A dermatoscopic image of a skin lesion.
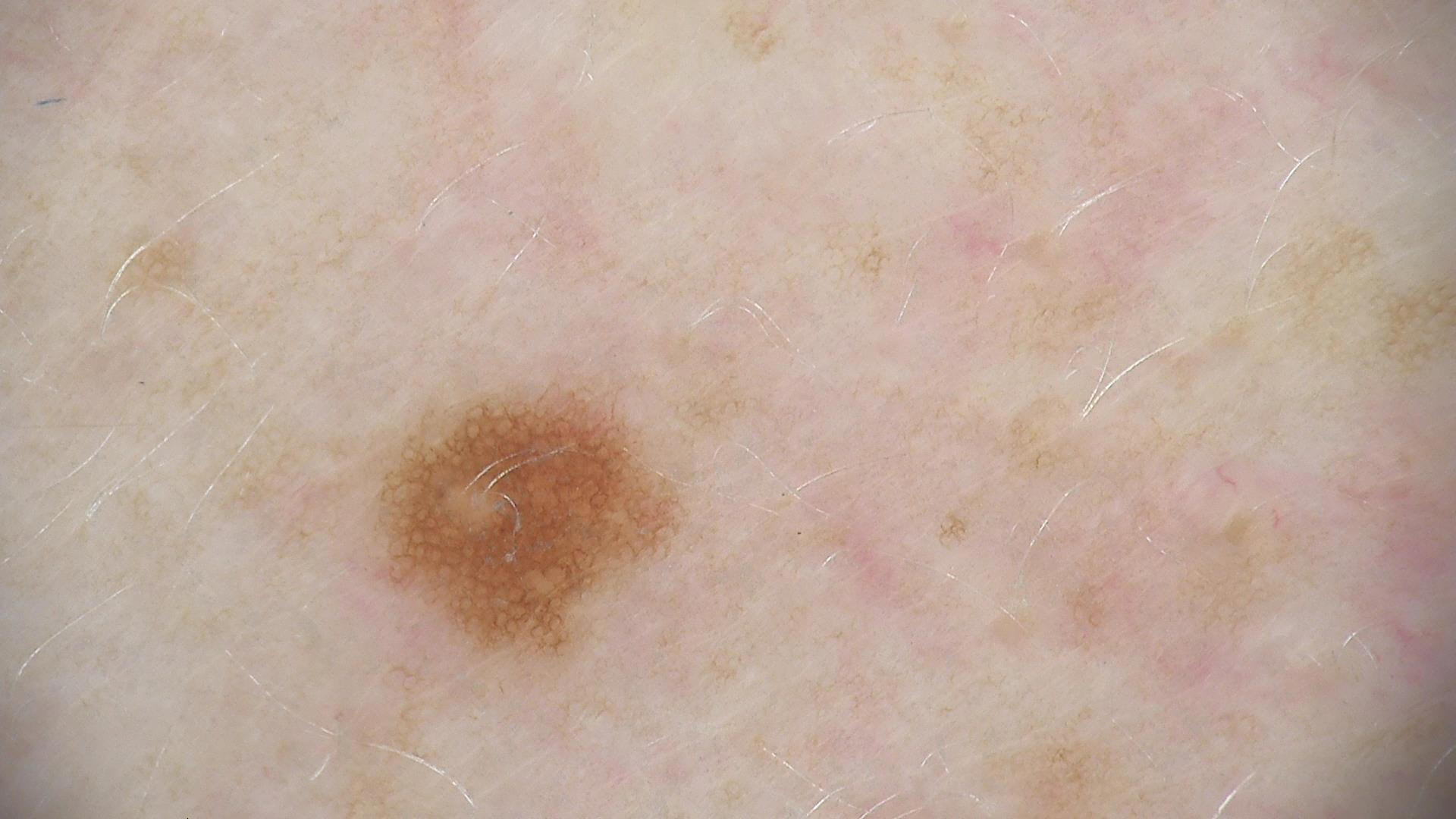The morphology is that of a banal lesion.
The diagnostic label was a junctional nevus.